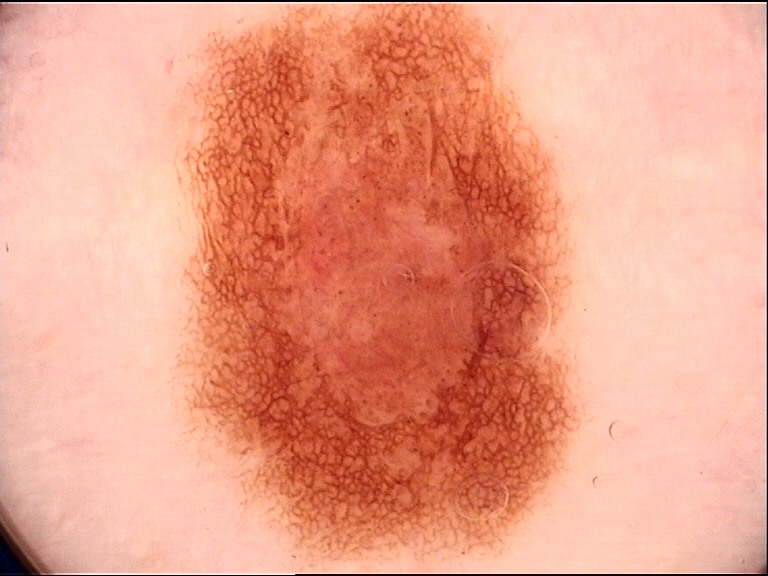label — dysplastic compound nevus (expert consensus)